A dermoscopic close-up of a skin lesion · the patient is FST II · a male patient in their mid- to late 60s — 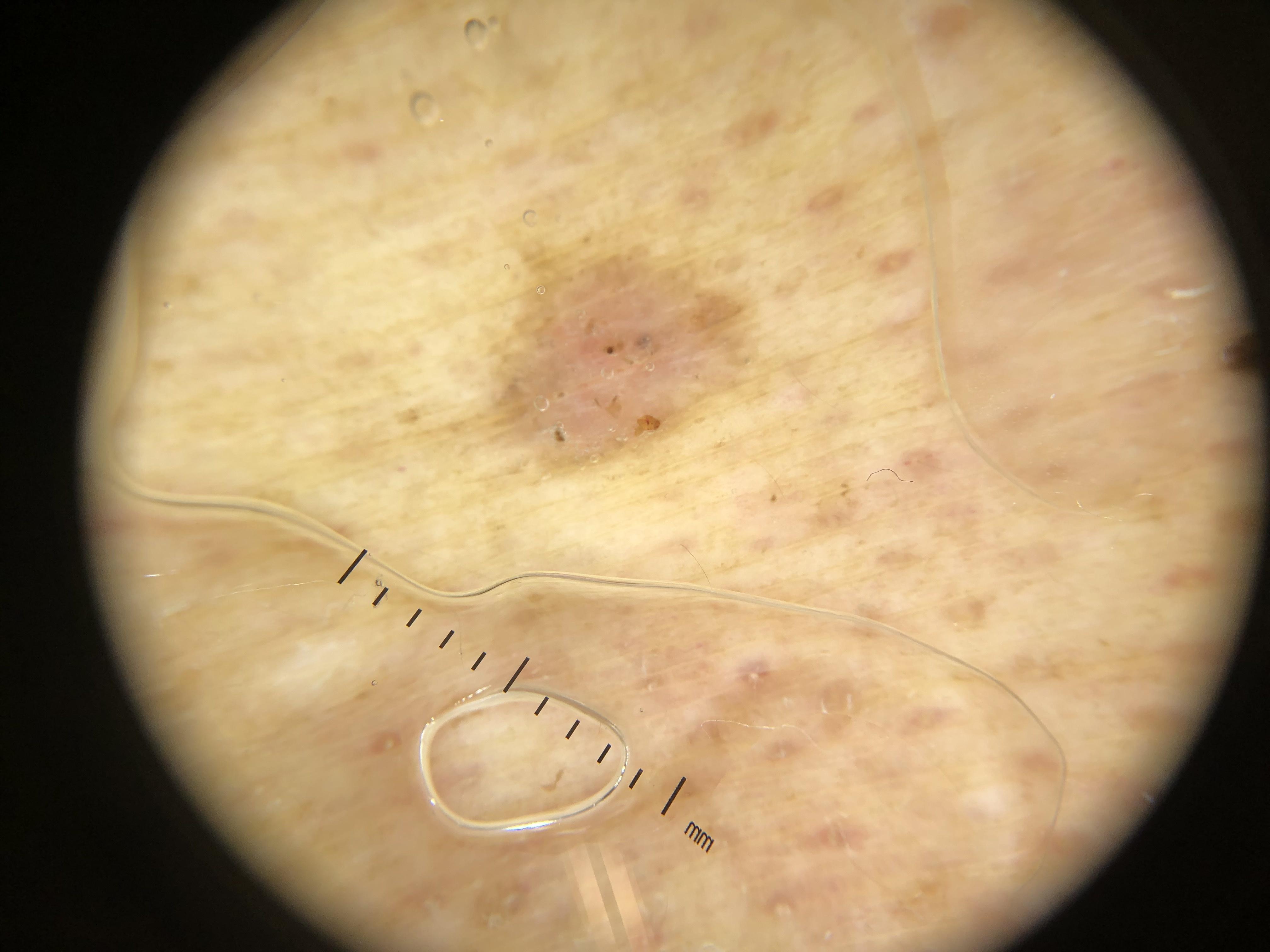Clinical context:
The lesion was found on the trunk.
Diagnosis:
Biopsy-confirmed as a malignant, adnexal lesion — a basal cell carcinoma.